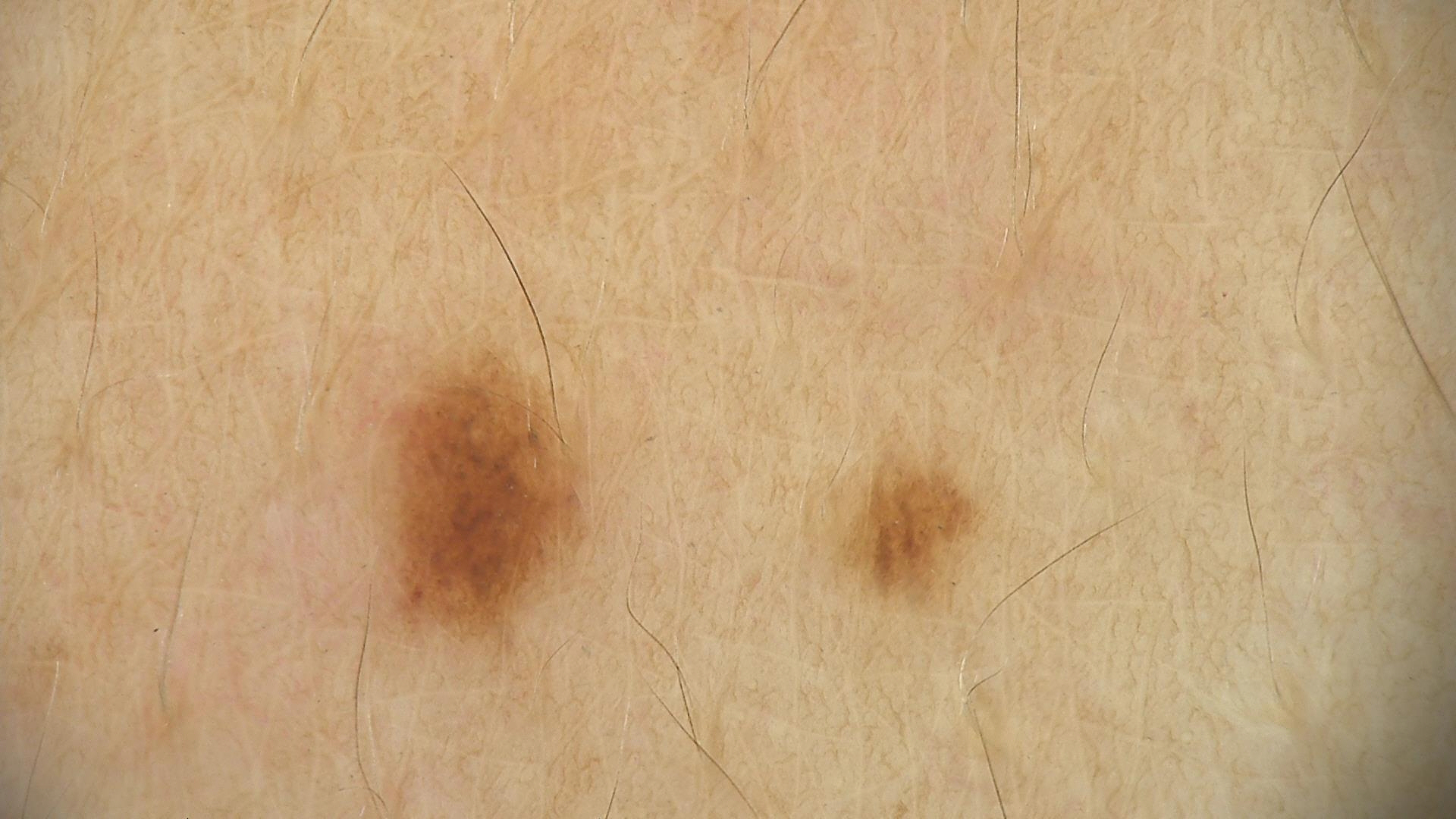Case:
A dermoscopic photograph of a skin lesion.
Conclusion:
The diagnosis was a dysplastic junctional nevus.